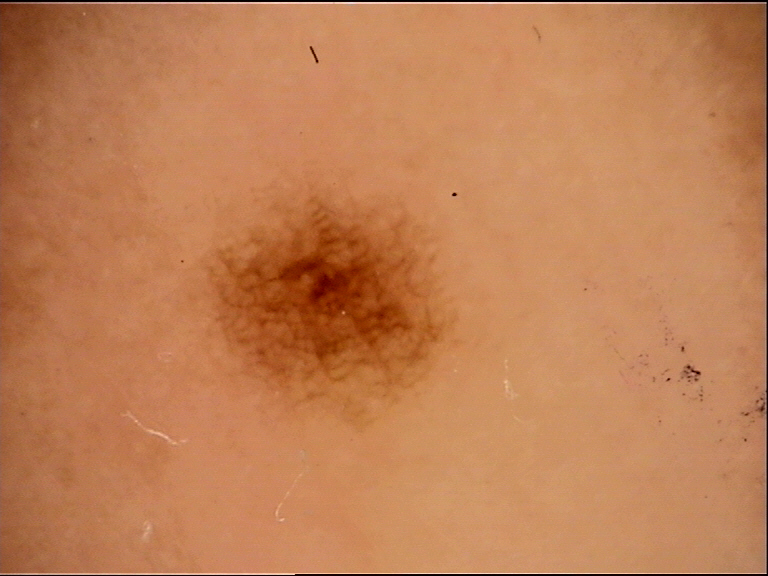imaging: dermatoscopy; diagnosis: acral junctional nevus (expert consensus).